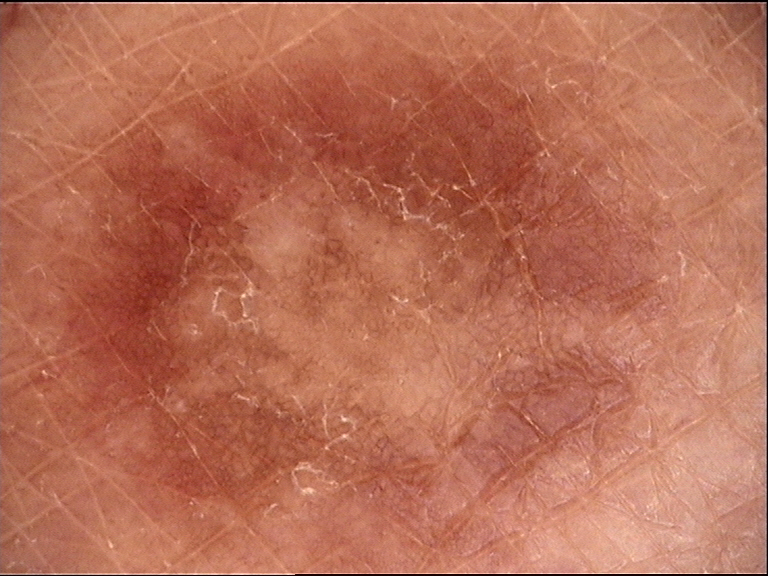modality: dermoscopy | subtype: fibro-histiocytic | assessment: dermatofibroma (expert consensus).